A subject in their late 70s: 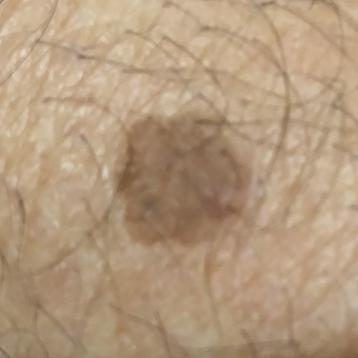The lesion was found on a thigh.
The patient describes that the lesion is elevated.
The consensus clinical diagnosis was a seborrheic keratosis.